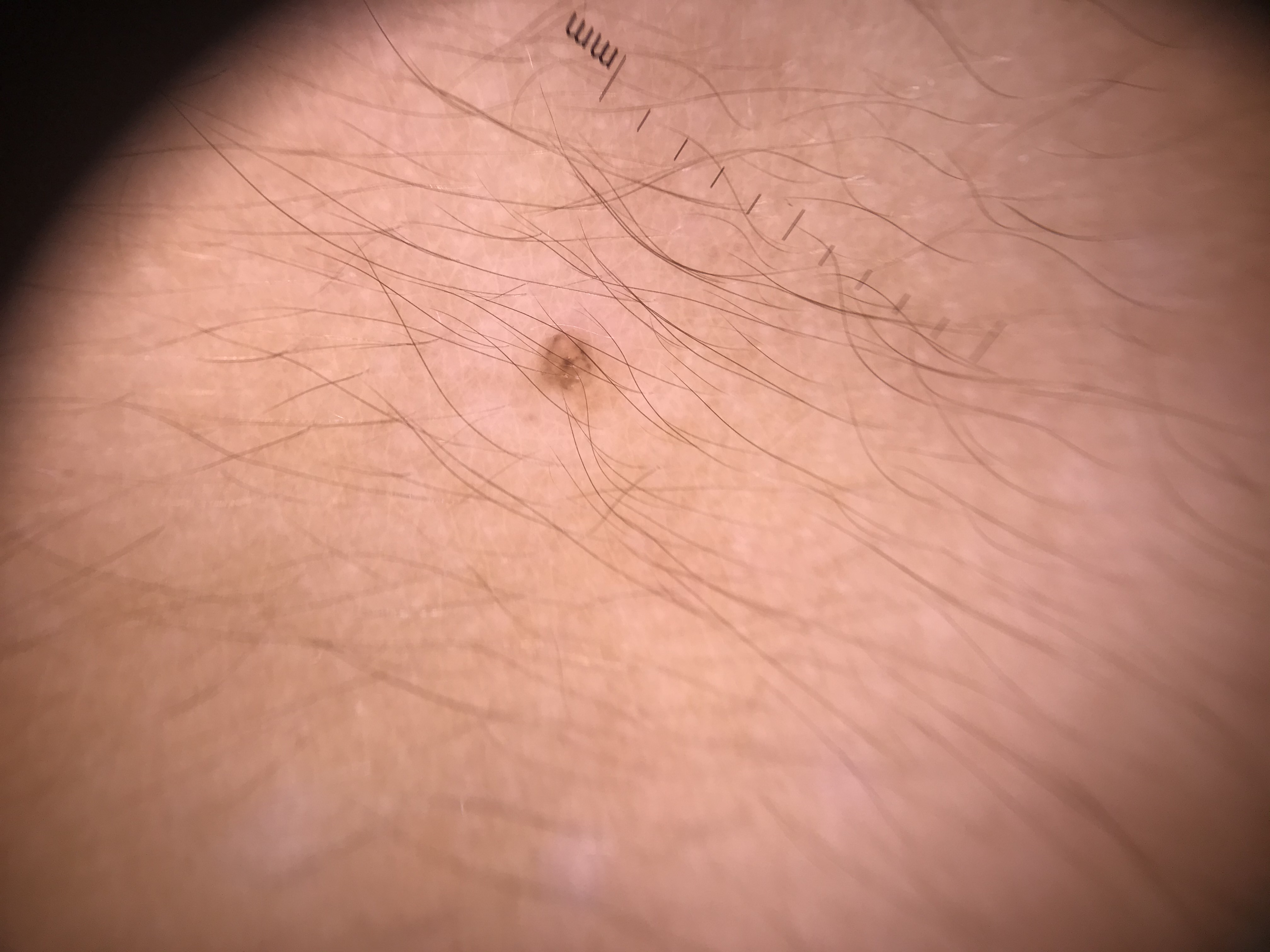Q: What is the imaging modality?
A: dermoscopy
Q: What kind of lesion is this?
A: banal
Q: What was the diagnostic impression?
A: junctional nevus (expert consensus)